A dermoscopic image of a skin lesion.
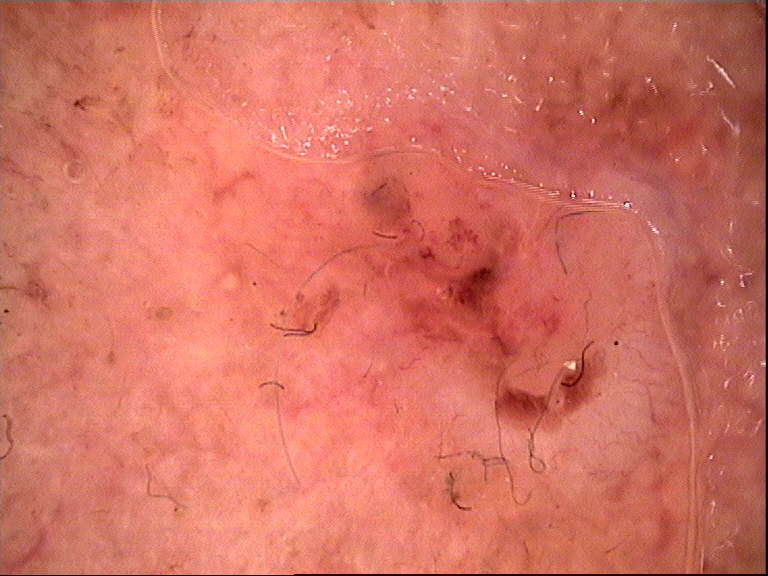The architecture is that of a keratinocytic lesion.
Biopsy-confirmed as a basal cell carcinoma.